A close-up photograph:
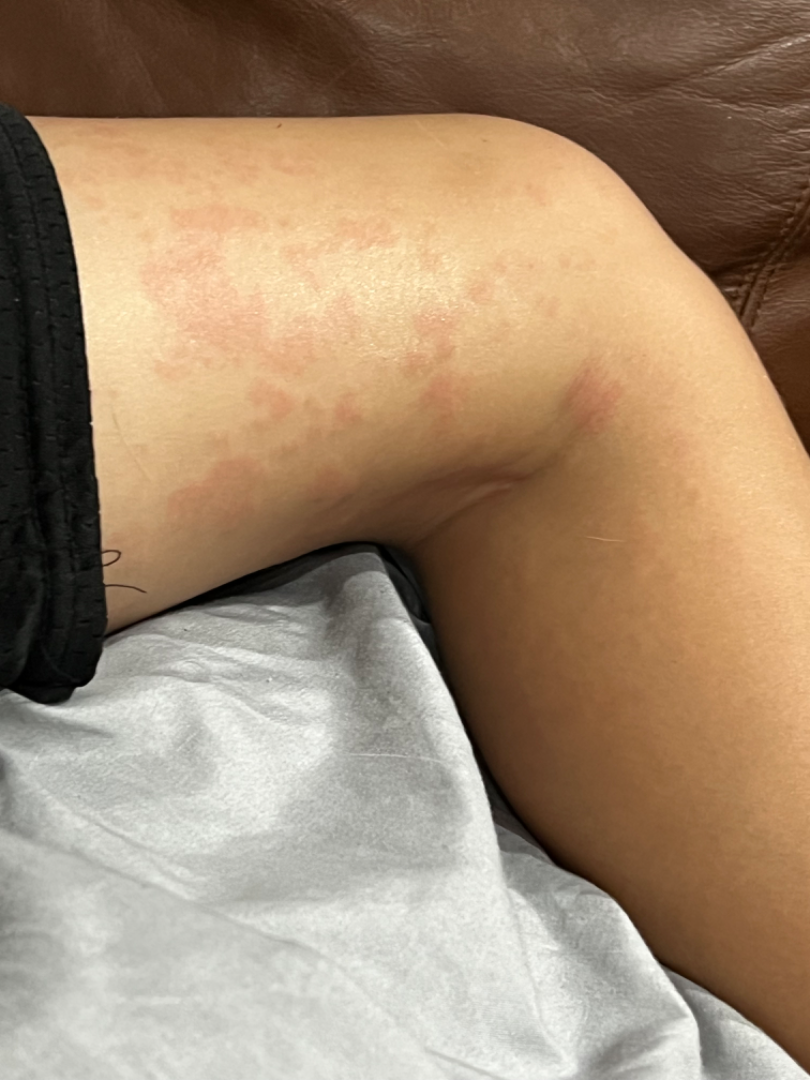On teledermatology review: the impression on review was Urticaria.